A subject age 63; a clinical photograph showing a skin lesion — 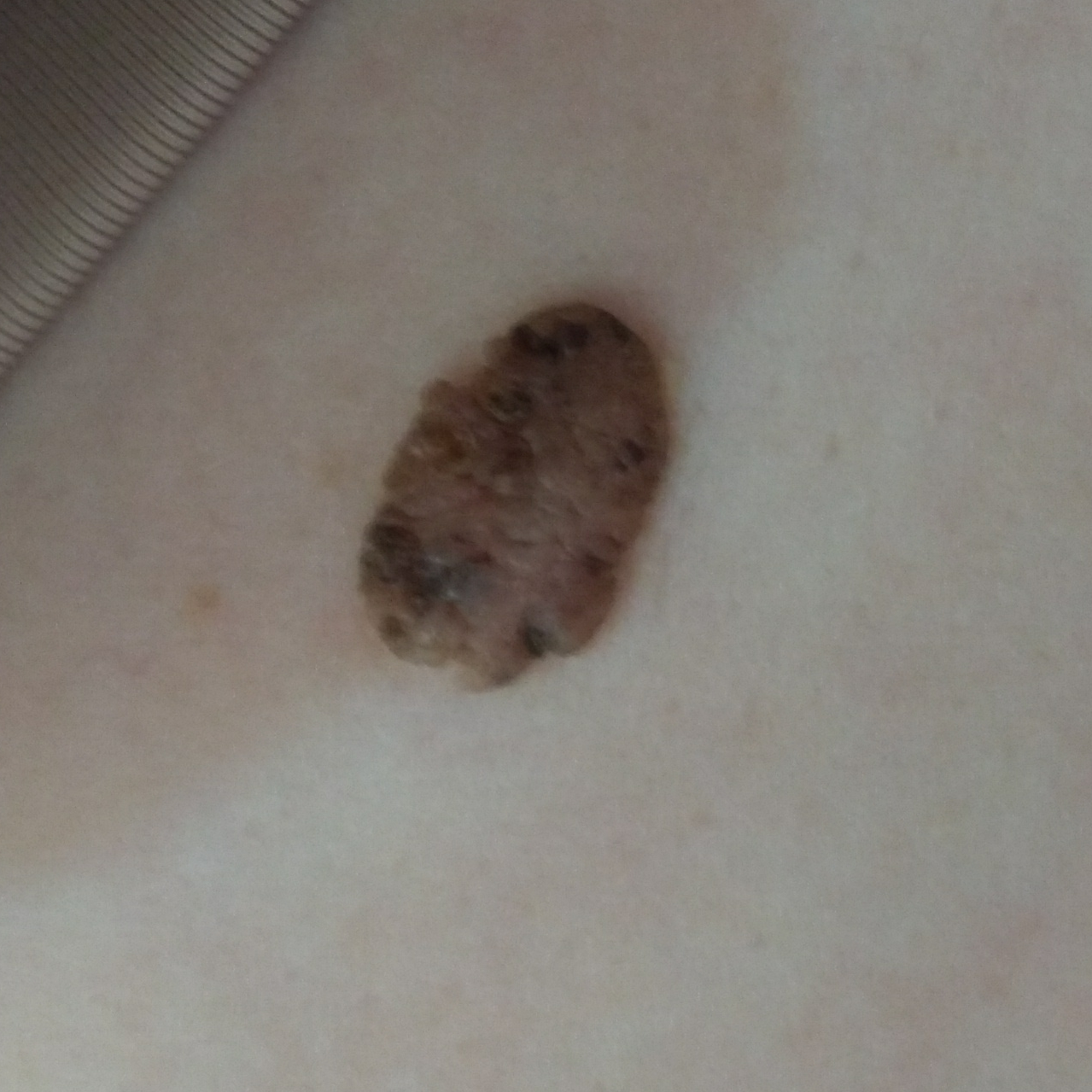{"lesion_location": "the abdomen", "symptoms": {"present": ["elevation"]}, "diagnosis": {"name": "seborrheic keratosis", "code": "SEK", "malignancy": "benign", "confirmation": "clinical consensus"}}